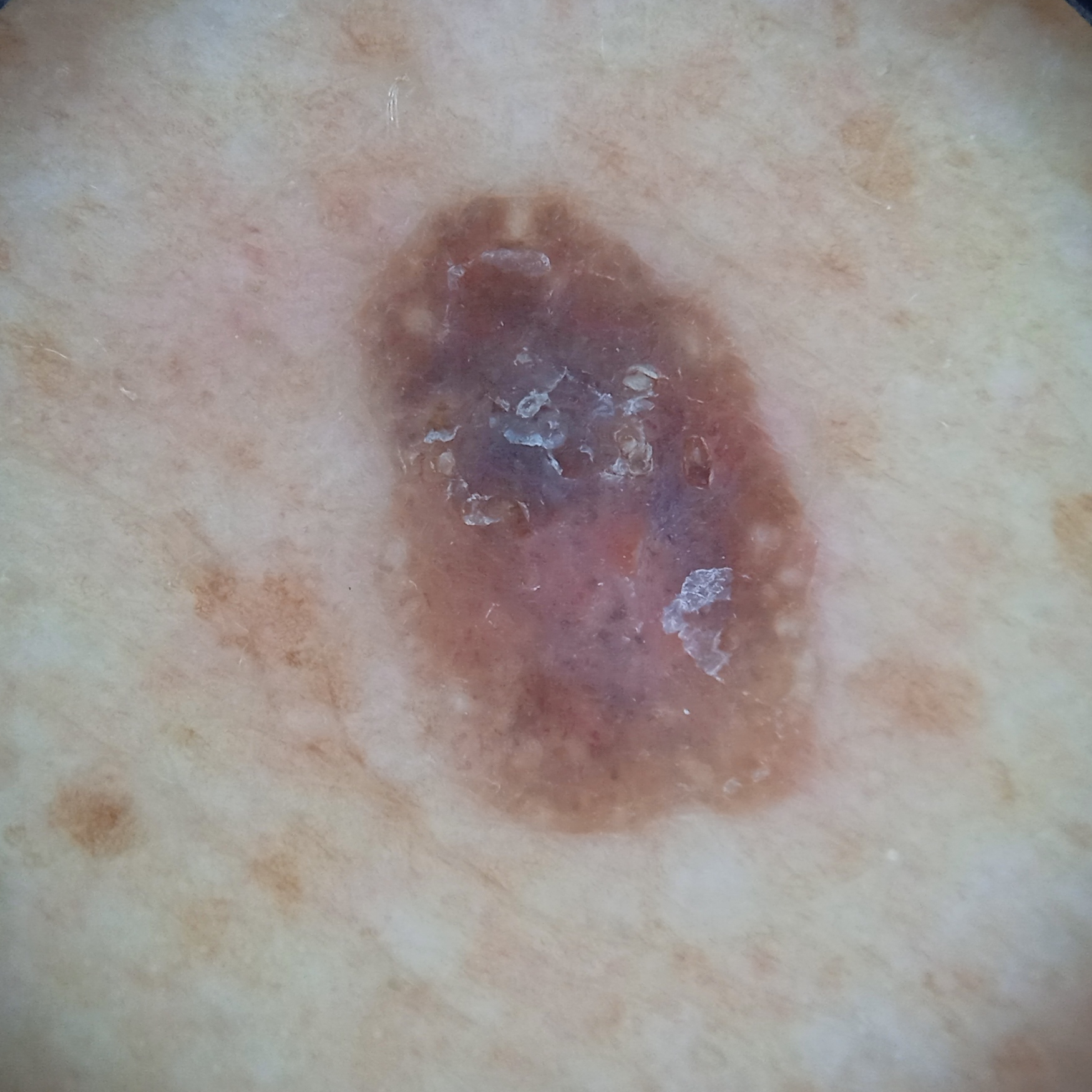patient — male, 72 years old; sun reaction — skin tans without first burning; image type — dermoscopy; referral context — research study (no referral diagnosis); location — the back; lesion size — 8.1 mm; diagnostic label — seborrheic keratosis (dermatologist consensus).